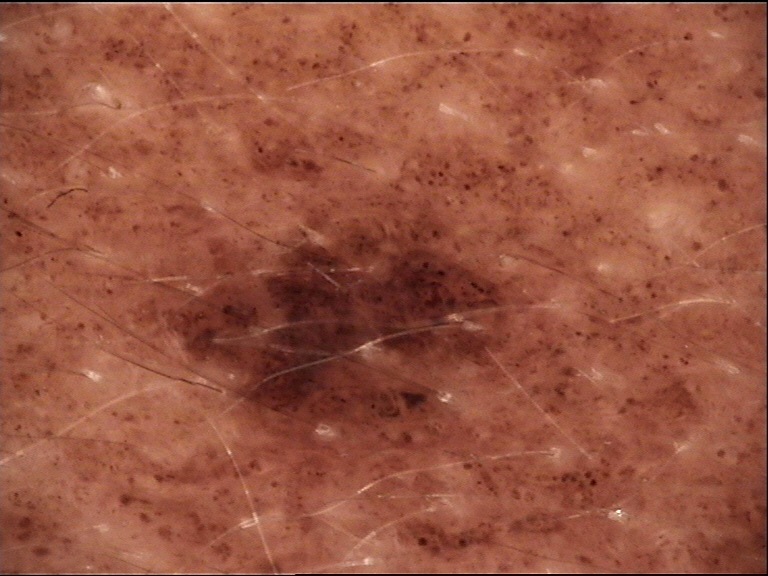The architecture is that of a banal lesion.
Consistent with a congenital compound nevus.